A female patient, aged approximately 30. A dermoscopic view of a skin lesion.
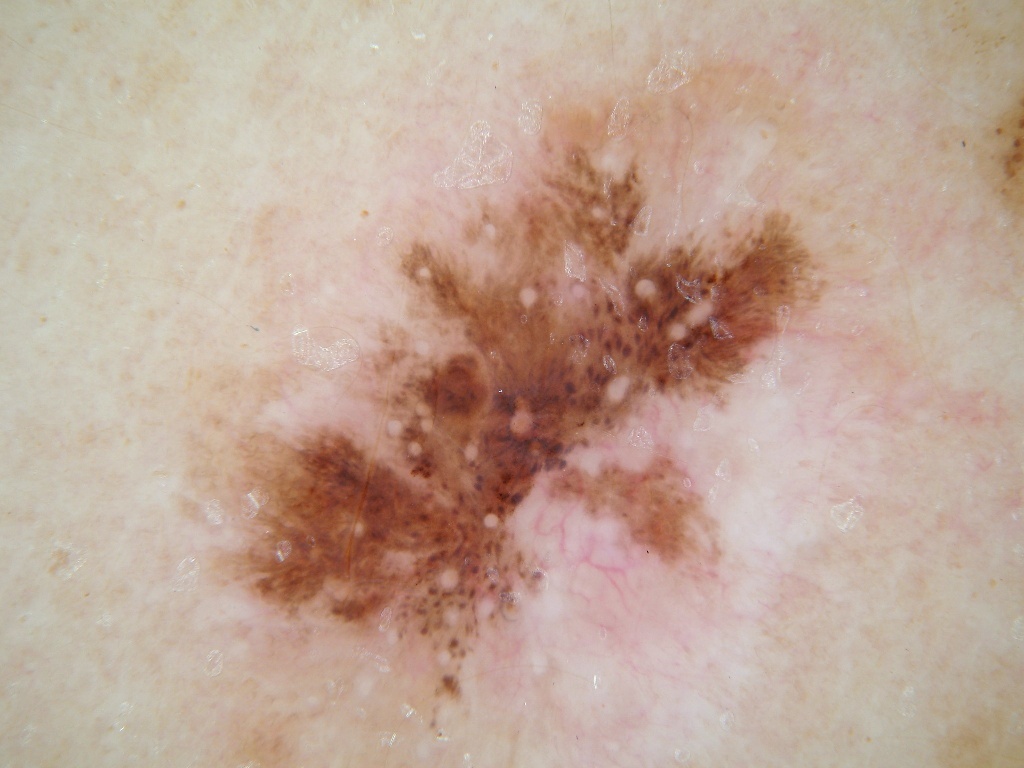Summary:
Dermoscopy demonstrates milia-like cysts, pigment network, and globules; no negative network or streaks. The lesion takes up about 33% of the image. The visible lesion spans [184, 110, 858, 748].
Conclusion:
Clinically diagnosed as a melanocytic nevus.